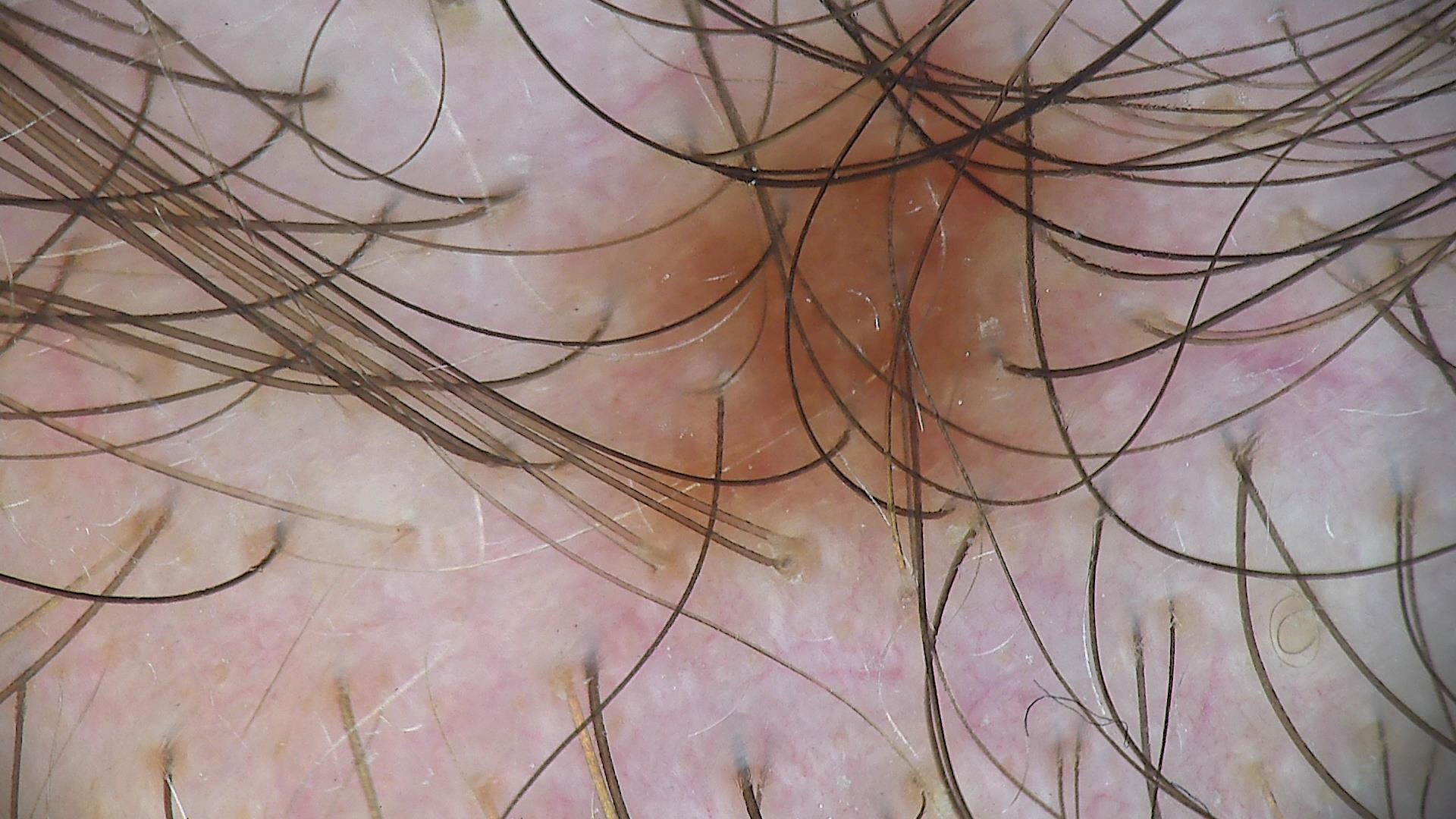Q: What kind of image is this?
A: dermoscopy
Q: What is this lesion?
A: dysplastic junctional nevus (expert consensus)